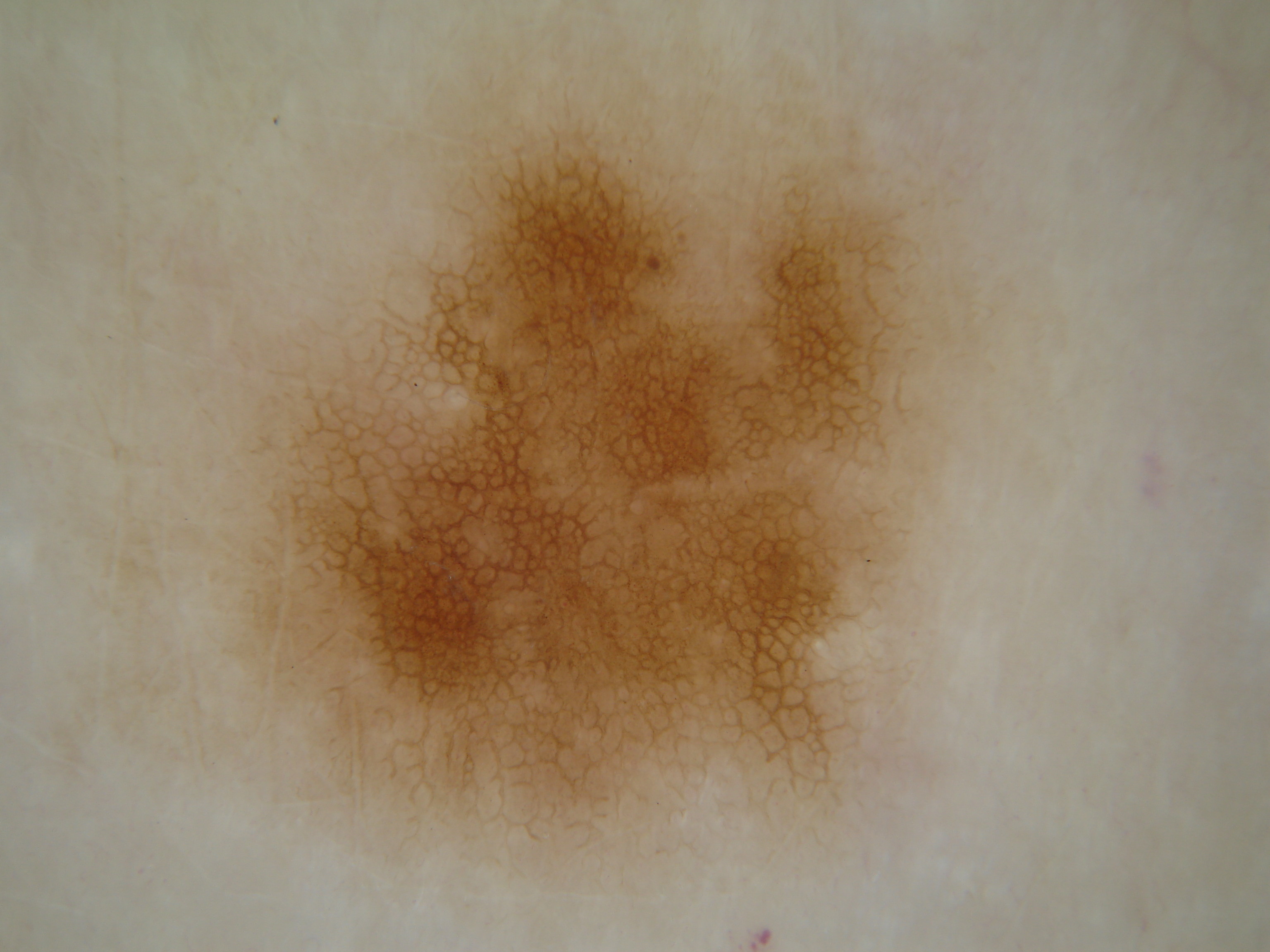A dermoscopic close-up of a skin lesion. The dermoscopic pattern shows globules; no streaks. With coordinates (x1, y1, x2, y2), the lesion spans <box>167, 20, 1001, 861</box>. Expert review diagnosed this as a benign skin lesion.